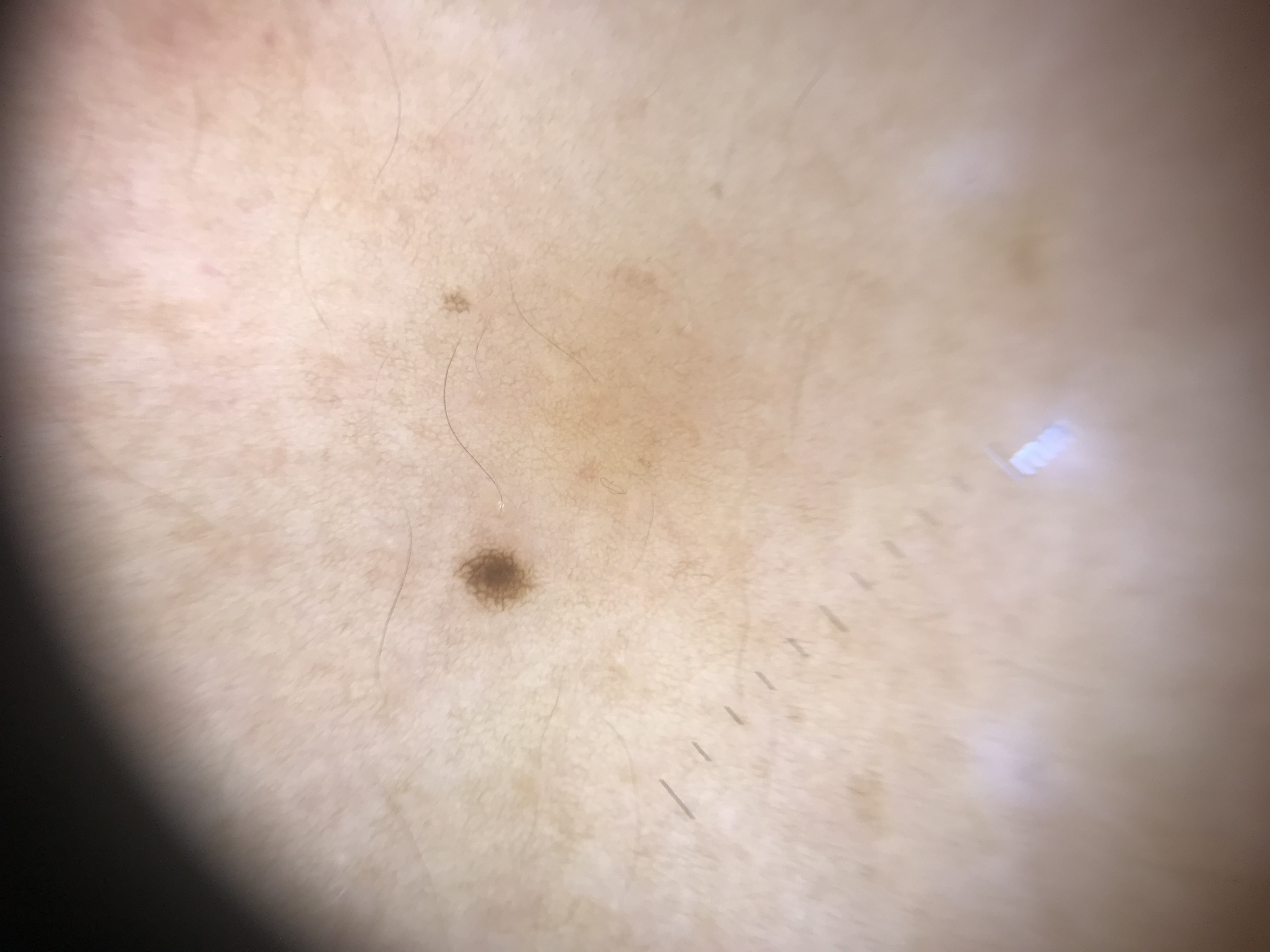Q: What is the imaging modality?
A: dermoscopy
Q: What is this lesion?
A: junctional nevus (expert consensus)